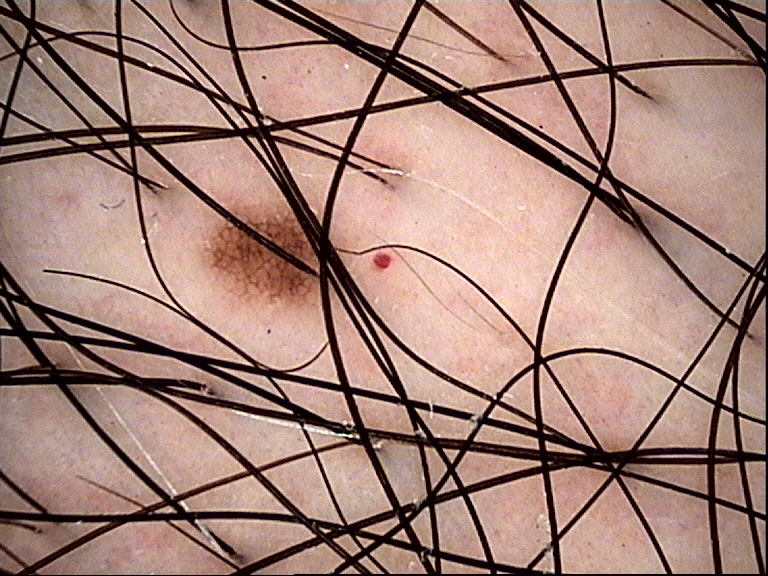Dermoscopy of a skin lesion.
This is a banal lesion.
Classified as a junctional nevus.